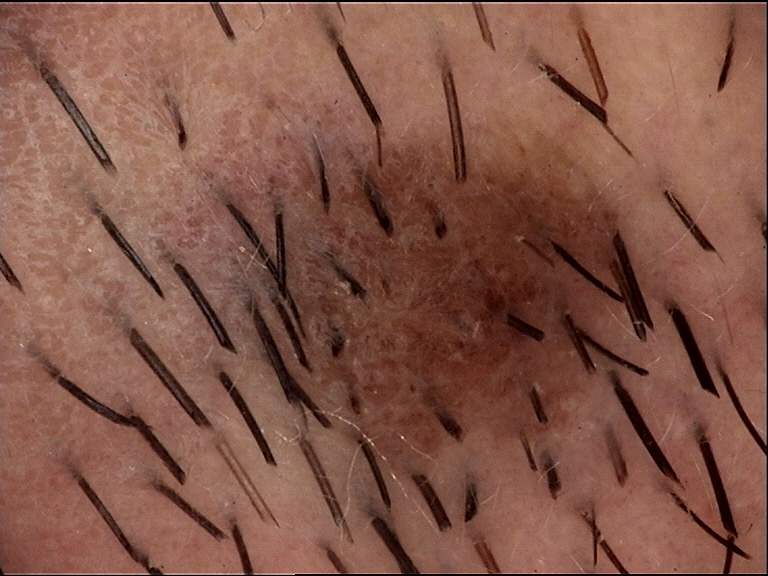Q: What is the lesion category?
A: banal
Q: What was the diagnostic impression?
A: compound nevus (expert consensus)